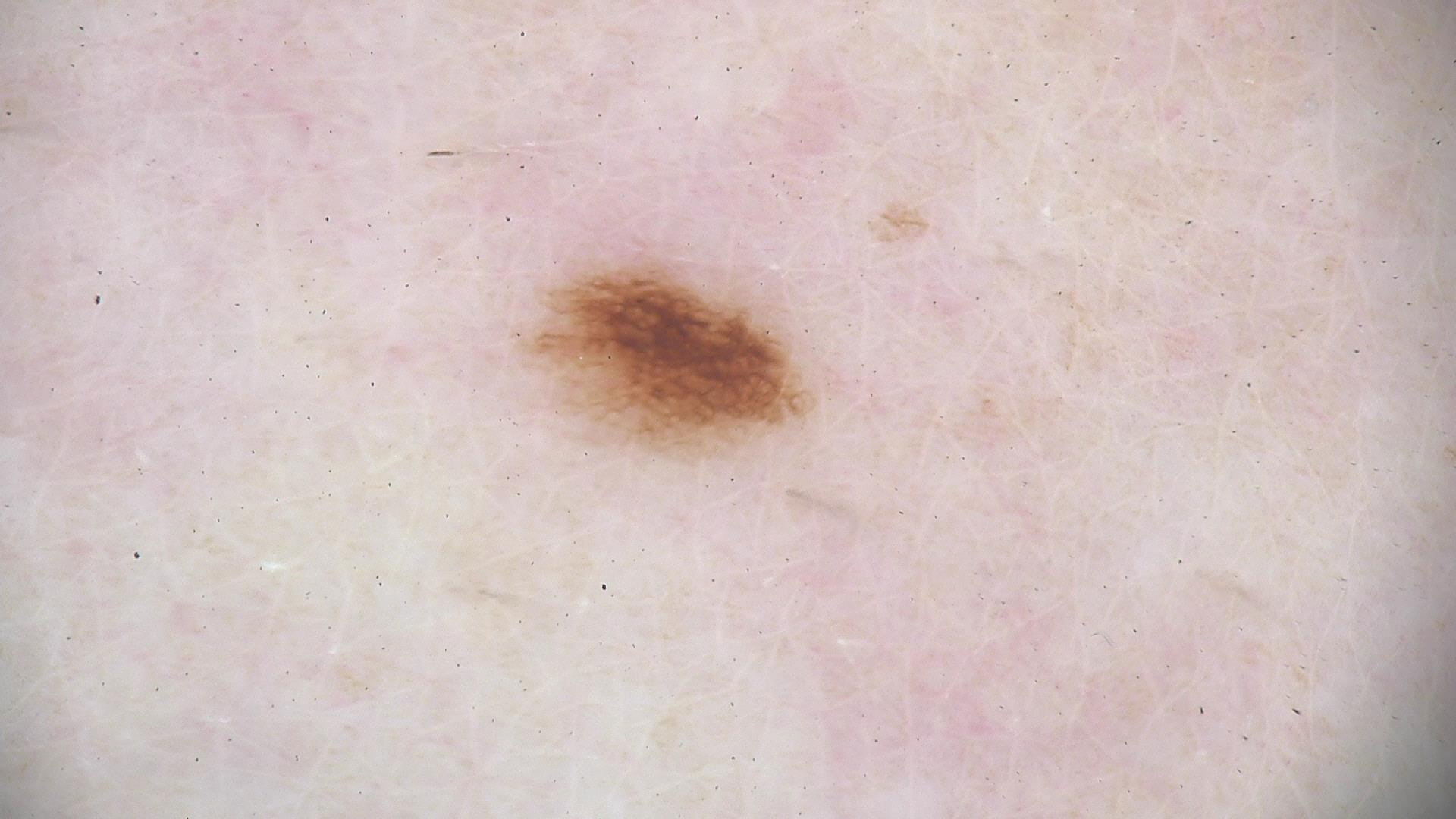Impression: The diagnosis was a dysplastic junctional nevus.